Imaged for a research study, with no referral diagnosis recorded. The patient reports a personal history of skin cancer, a personal history of cancer, and no sunbed use. The patient says their skin tans without first burning. A dermoscopy image of a skin lesion. A female subject 75 years of age. A moderate number of moles by the patient's own estimate — 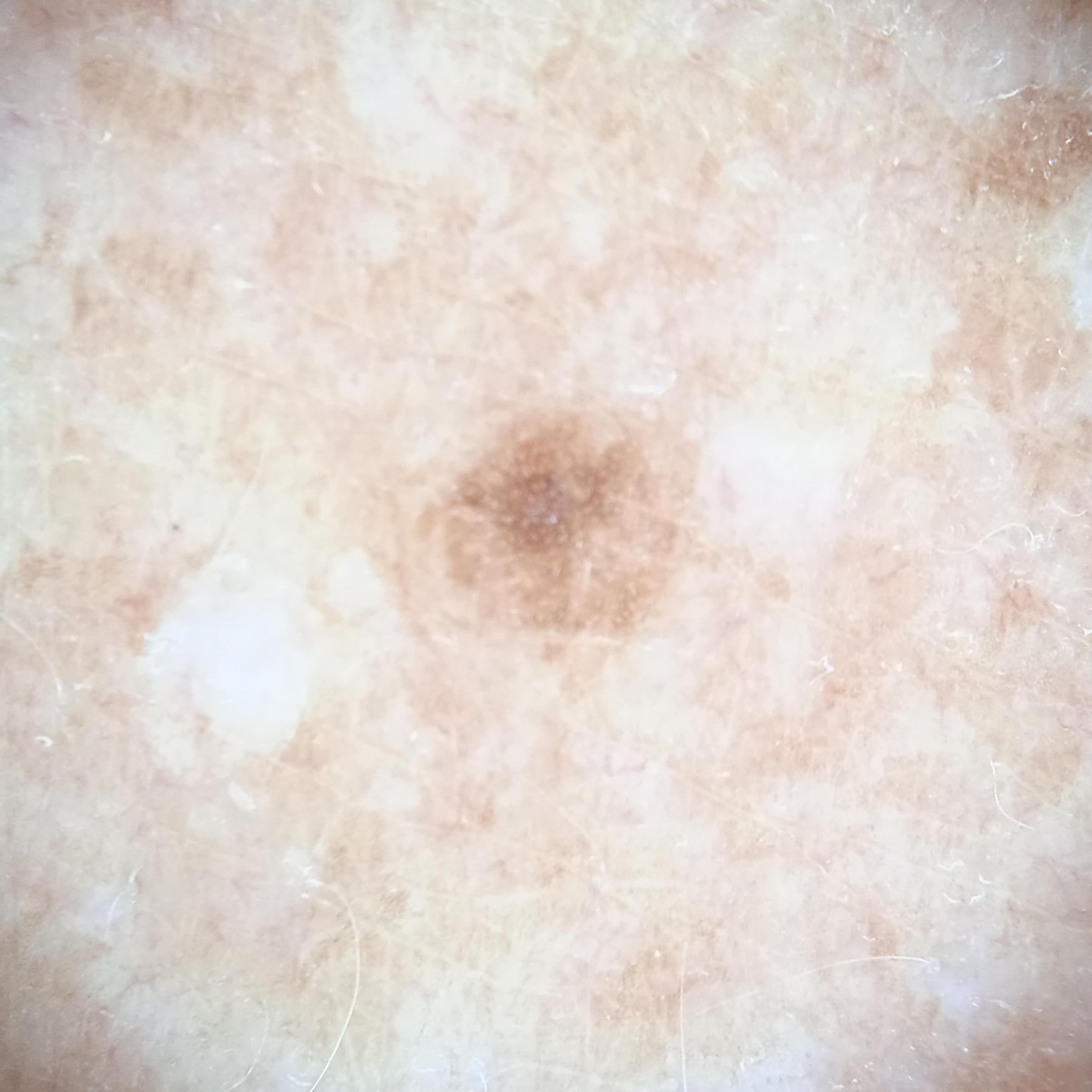body site: the back, size: 2.7 mm, diagnosis: melanocytic nevus (dermatologist consensus).